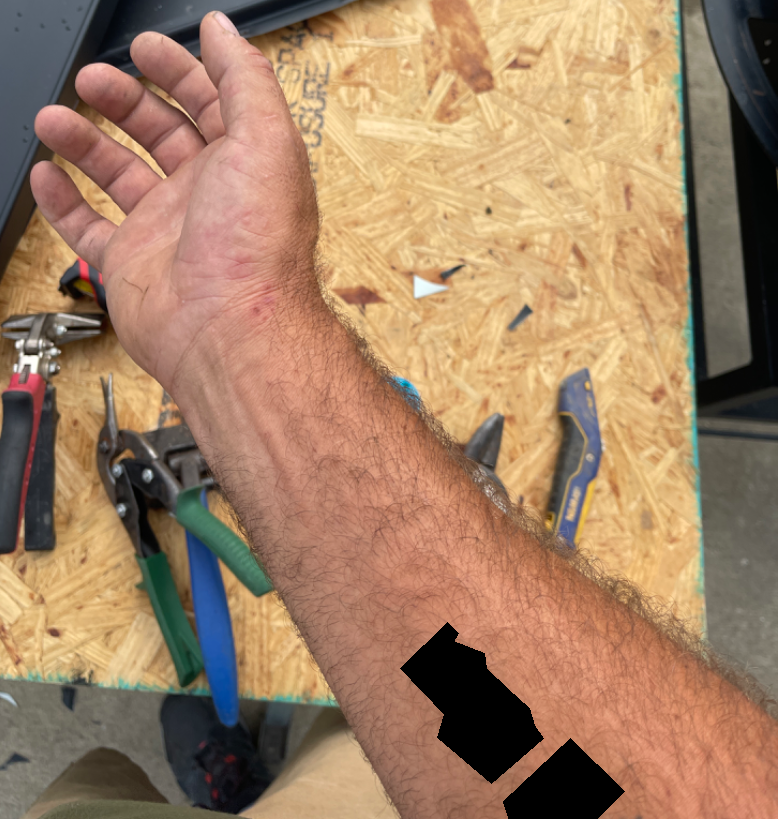Assessment: Single-reviewer assessment: favoring Eczema; with consideration of Scabies; also raised was Allergic Contact Dermatitis.